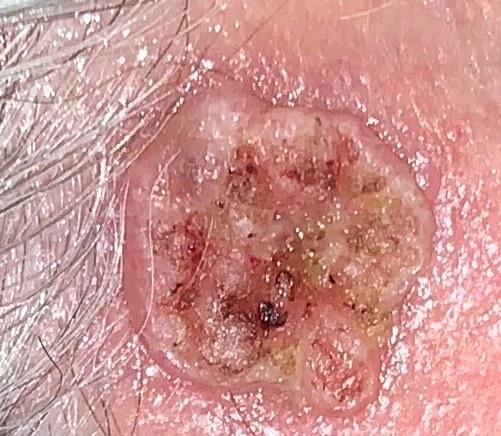pathology: Squamous cell carcinoma (biopsy-proven).